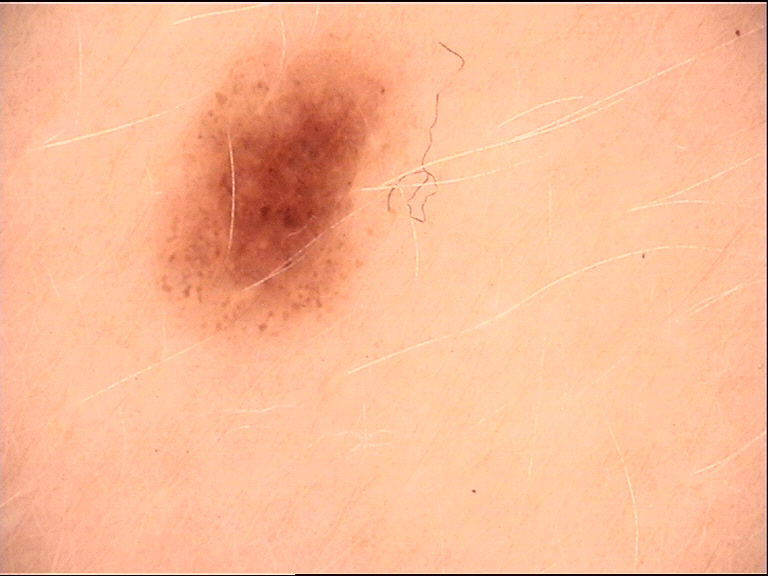{
  "diagnosis": {
    "name": "compound nevus",
    "code": "cb",
    "malignancy": "benign",
    "super_class": "melanocytic",
    "confirmation": "expert consensus"
  }
}